The patient is a male aged 18–29. Located on the arm, head or neck and front of the torso. This image was taken at an angle.
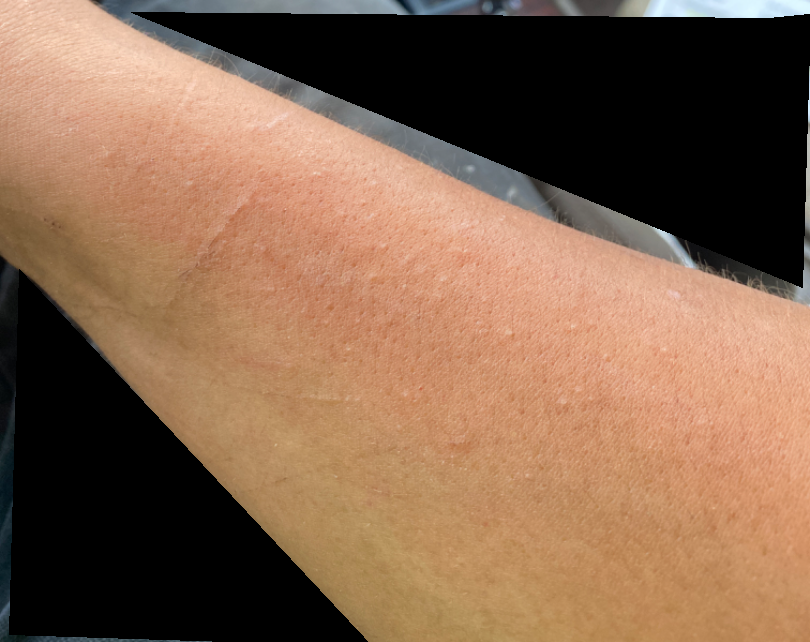symptoms:
  - itching
  - darkening
  - burning
patient_category: a rash
systemic_symptoms:
  - chills
  - fatigue
  - mouth sores
duration: less than one week
differential:
  leading:
    - Photodermatitis
  considered:
    - Urticaria
    - Allergic Contact Dermatitis
  unlikely:
    - Irritant Contact Dermatitis
    - Eczema